A dermoscopic close-up of a skin lesion.
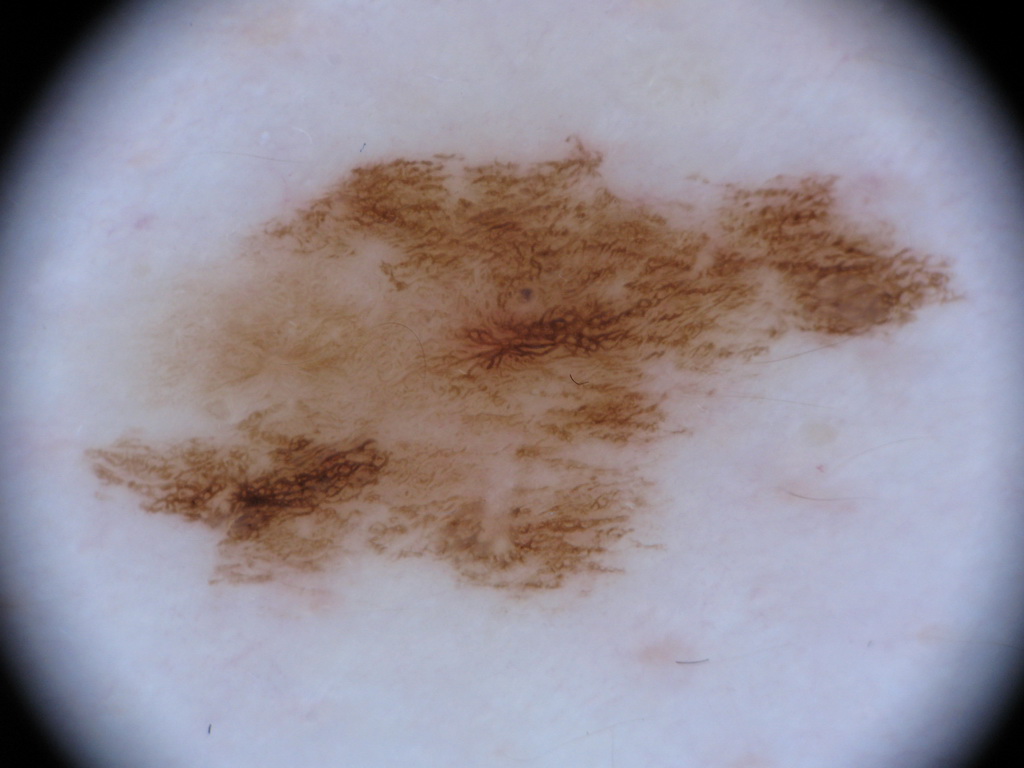Case summary: The lesion's extent is <box>80, 105, 960, 613</box>. The dermoscopic pattern shows pigment network, with no milia-like cysts, negative network, streaks, or globules. Conclusion: The diagnostic assessment was a melanocytic nevus, a benign skin lesion.